Self-categorized by the patient as a rash · the lesion involves the front of the torso · a close-up photograph · female patient, age 18–29: 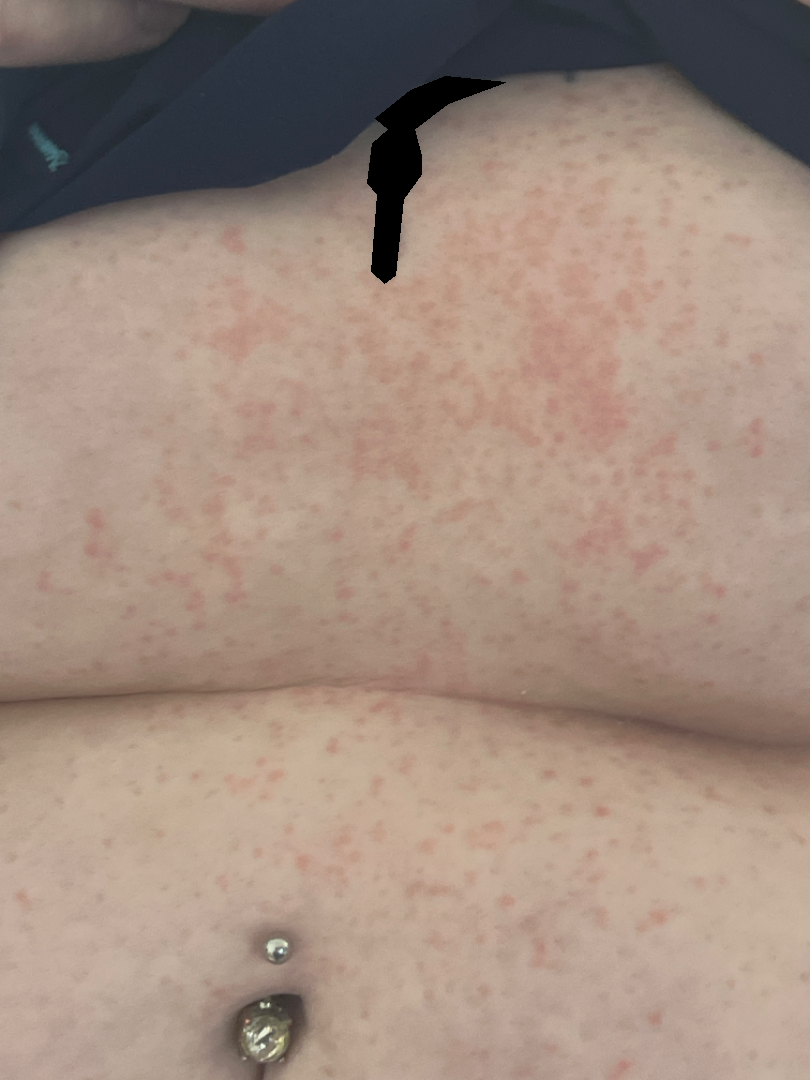On remote review of the image: Drug Rash (41%); Viral Exanthem (41%); Grover's disease (18%).